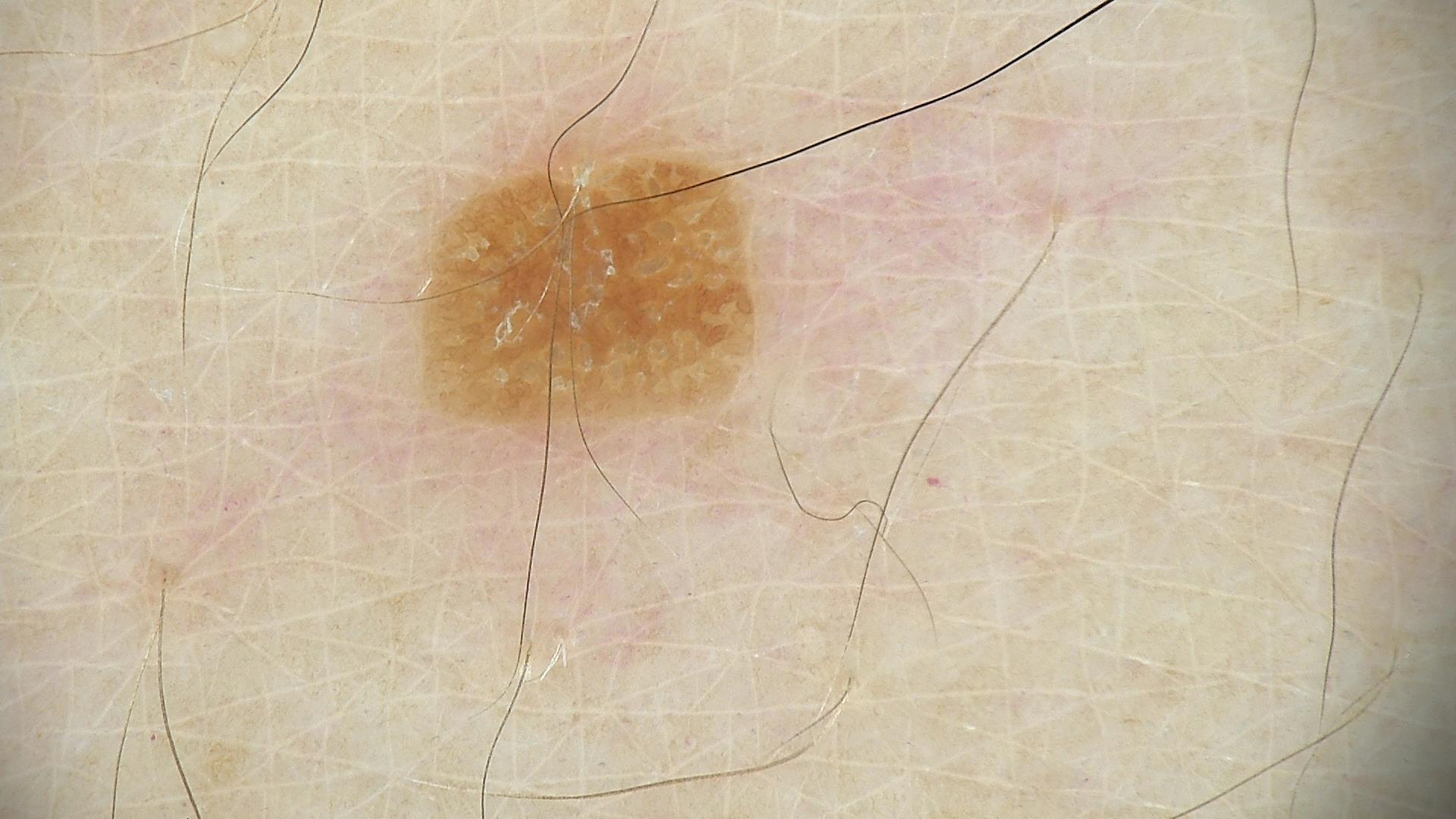Findings: A dermoscopic close-up of a skin lesion. Impression: The diagnostic label was a keratinocytic lesion — a seborrheic keratosis.